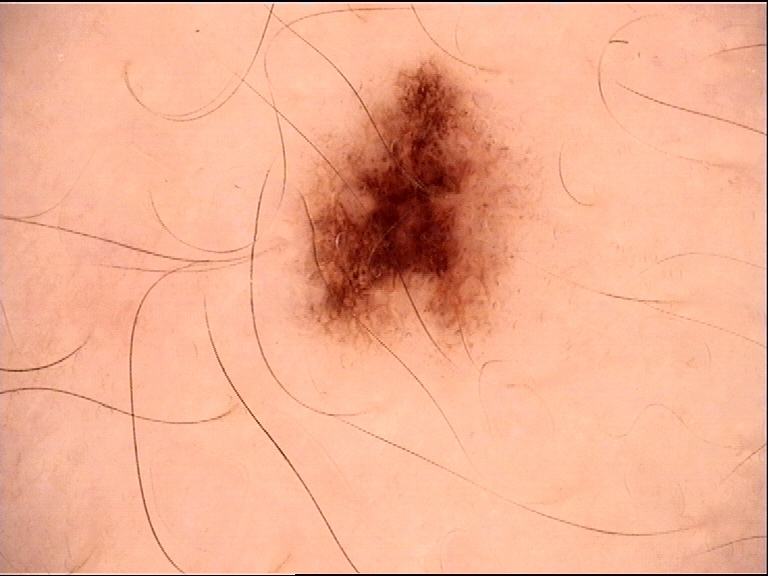Q: What kind of image is this?
A: dermoscopy
Q: What was the diagnostic impression?
A: dysplastic junctional nevus (expert consensus)